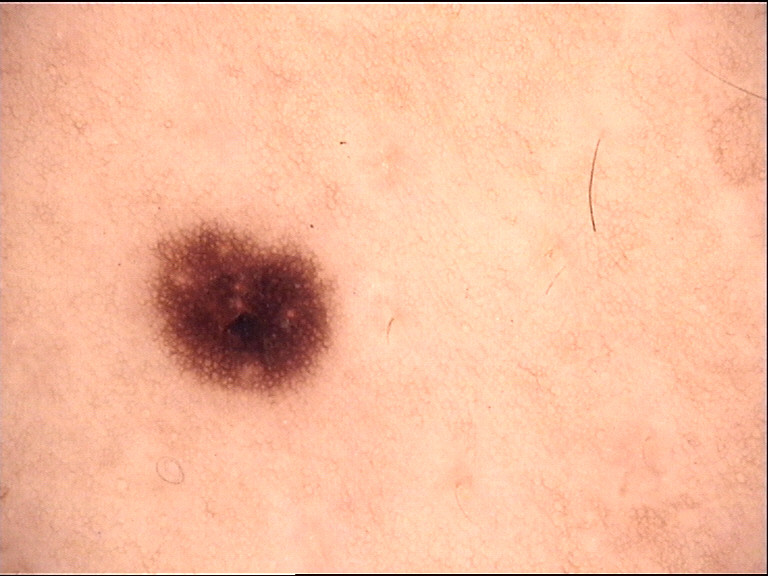| field | value |
|---|---|
| image type | dermatoscopy |
| diagnostic label | junctional nevus (expert consensus) |